A clinical photograph of a skin lesion; a subject age 58 — 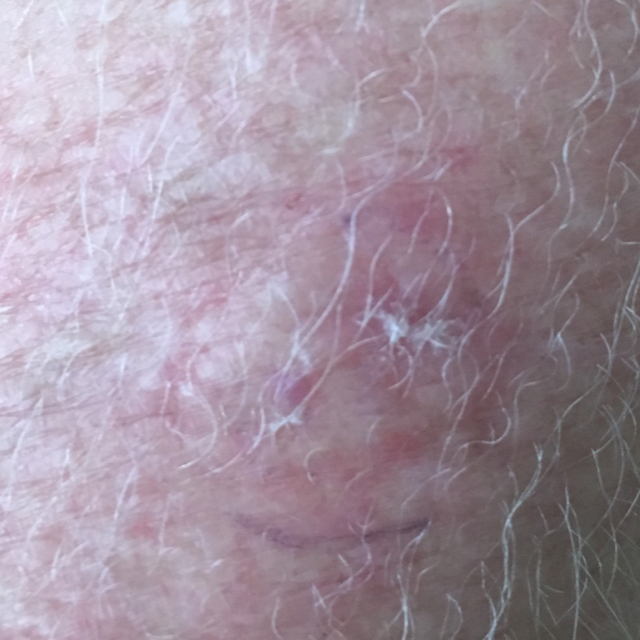Findings: The lesion is located on a forearm. The patient reports that the lesion itches. Impression: Clinically diagnosed as a lesion with uncertain malignant potential — an actinic keratosis.